A female patient roughly 55 years of age; dermoscopy of a skin lesion; recorded as Fitzpatrick skin type IV — 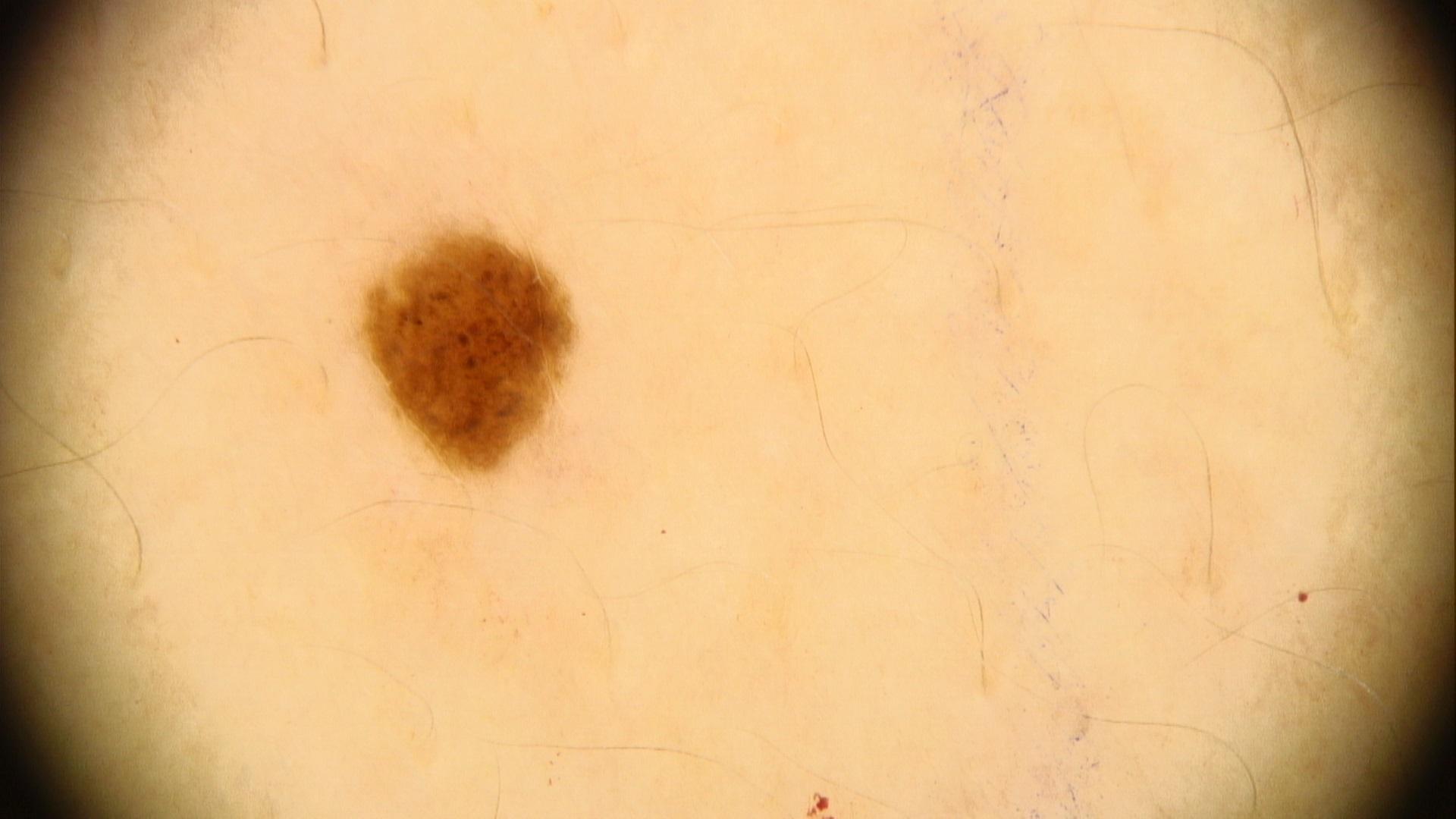Q: Where on the body is the lesion?
A: the trunk (the posterior trunk)
Q: What is the diagnosis?
A: Nevus